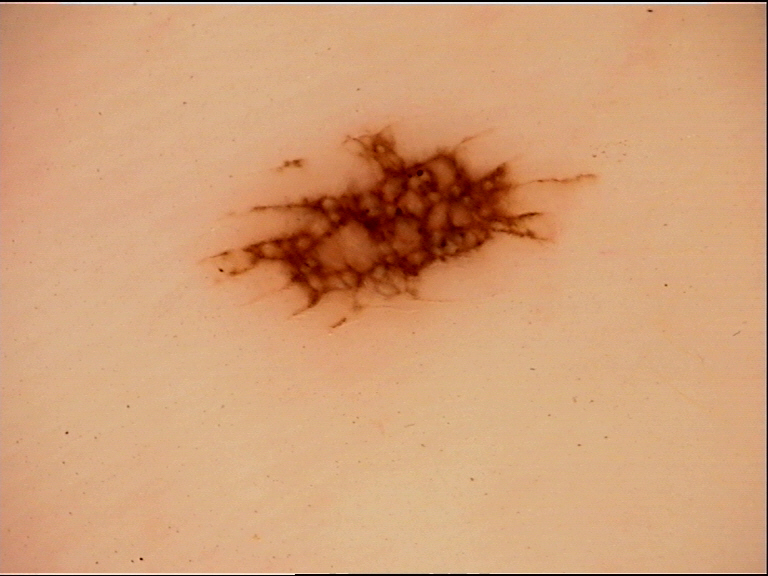Dermoscopy of a skin lesion.
This is a banal lesion.
Consistent with an acral junctional nevus.